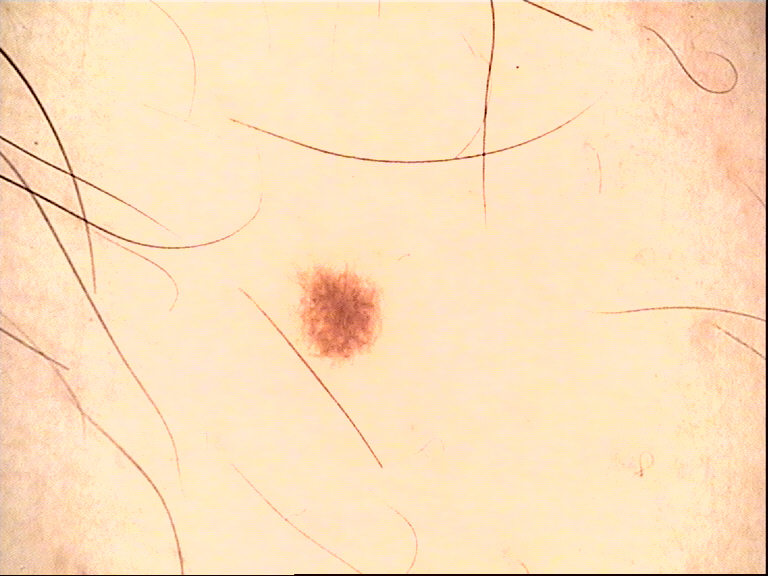Diagnosed as a junctional nevus.